The affected area is the leg. An image taken at a distance.
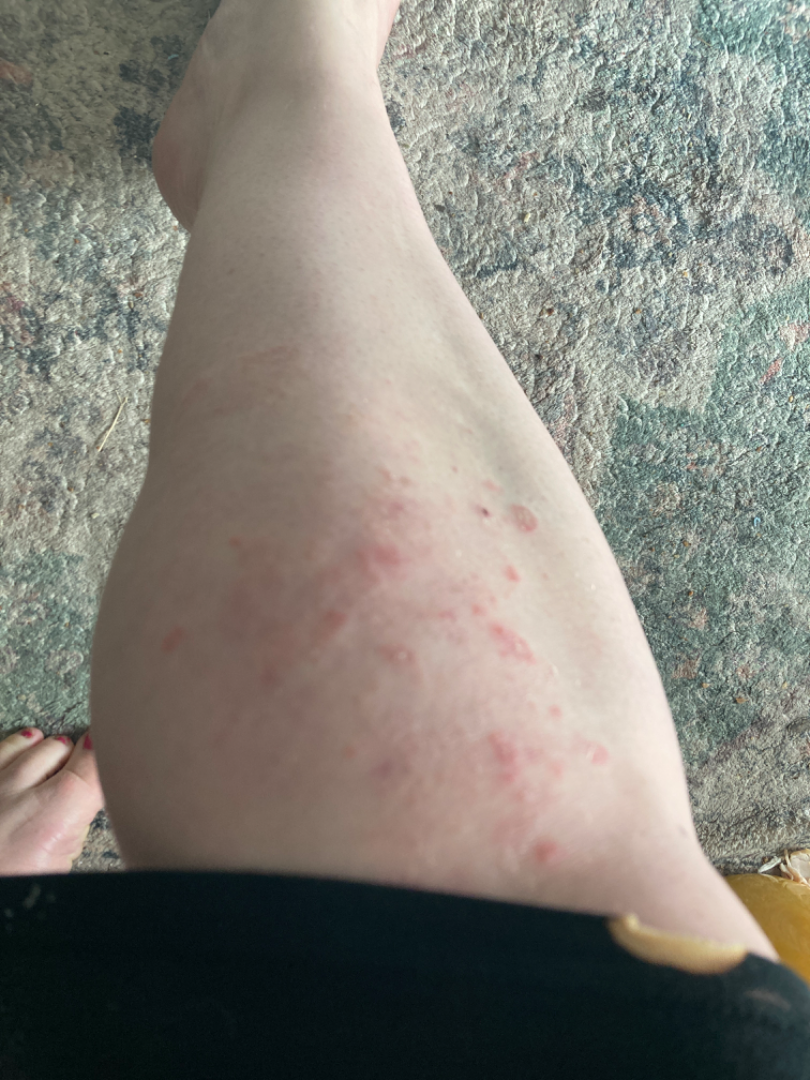Impression: The favored diagnosis is Tinea; with consideration of Psoriasis; lower on the differential is Granuloma annulare.